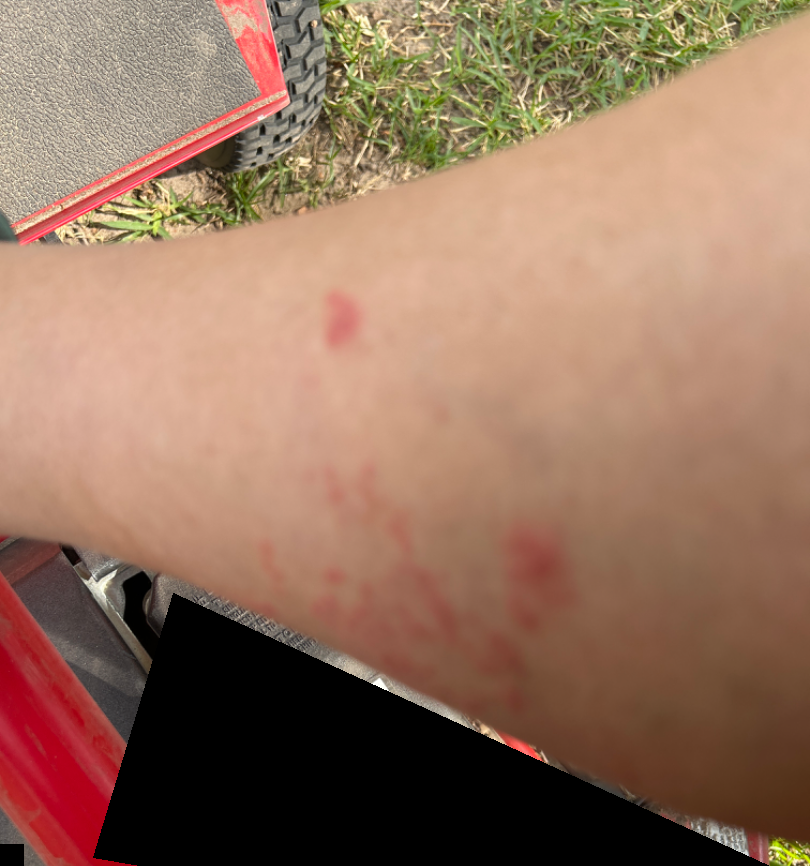Diagnostic features were not clearly distinguishable in this photograph. The contributor is 50–59, female. The photo was captured at an angle. The leg is involved.